The patient says their skin reddens with sun exposure · a dermatoscopic image of a skin lesion · by self-report, a personal history of cancer · a male subject aged 73 · imaged for a research study, with no referral diagnosis recorded · the patient describes having numerous moles — 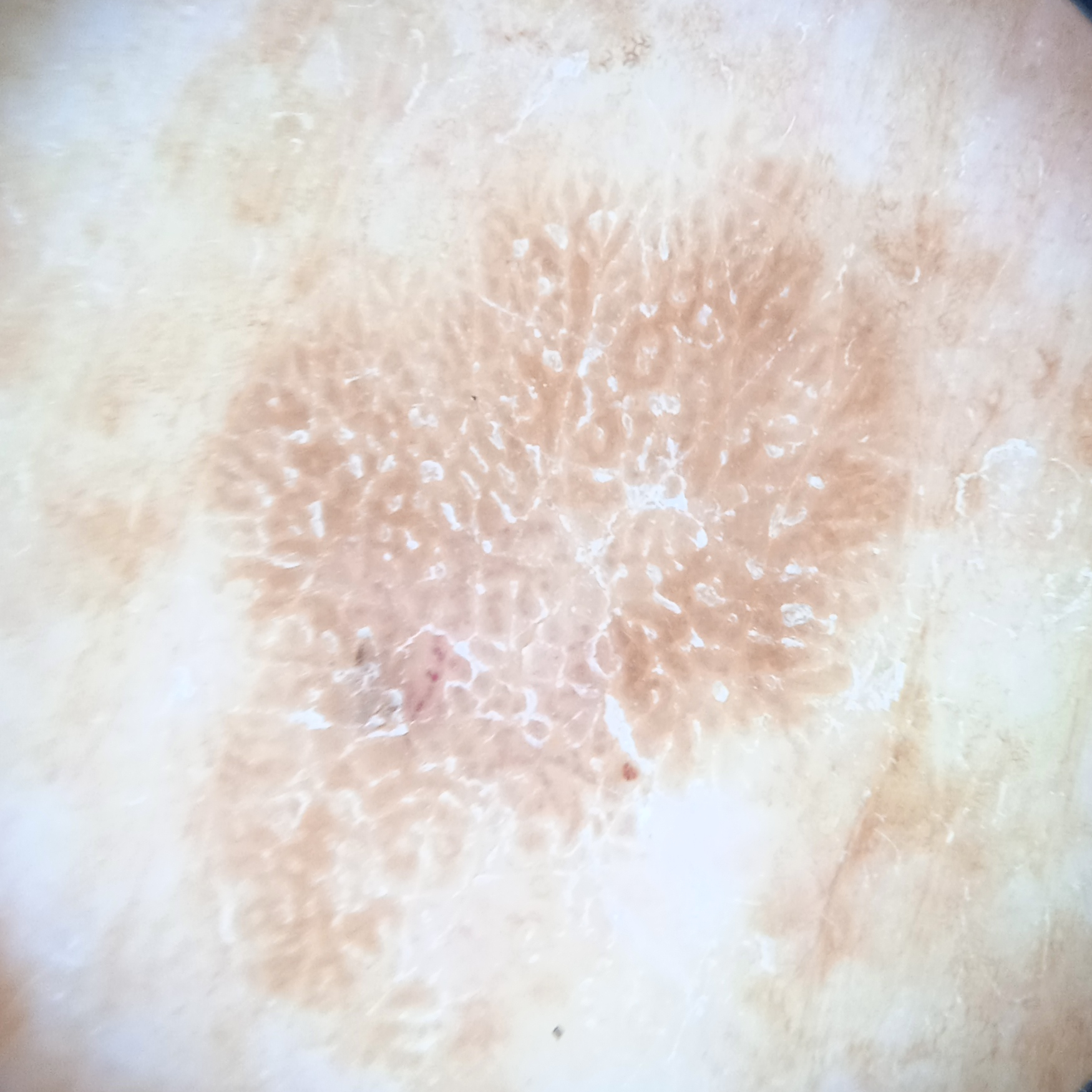The lesion is on the back. Measuring roughly 10.7 mm. The consensus diagnosis for this lesion was a seborrheic keratosis.